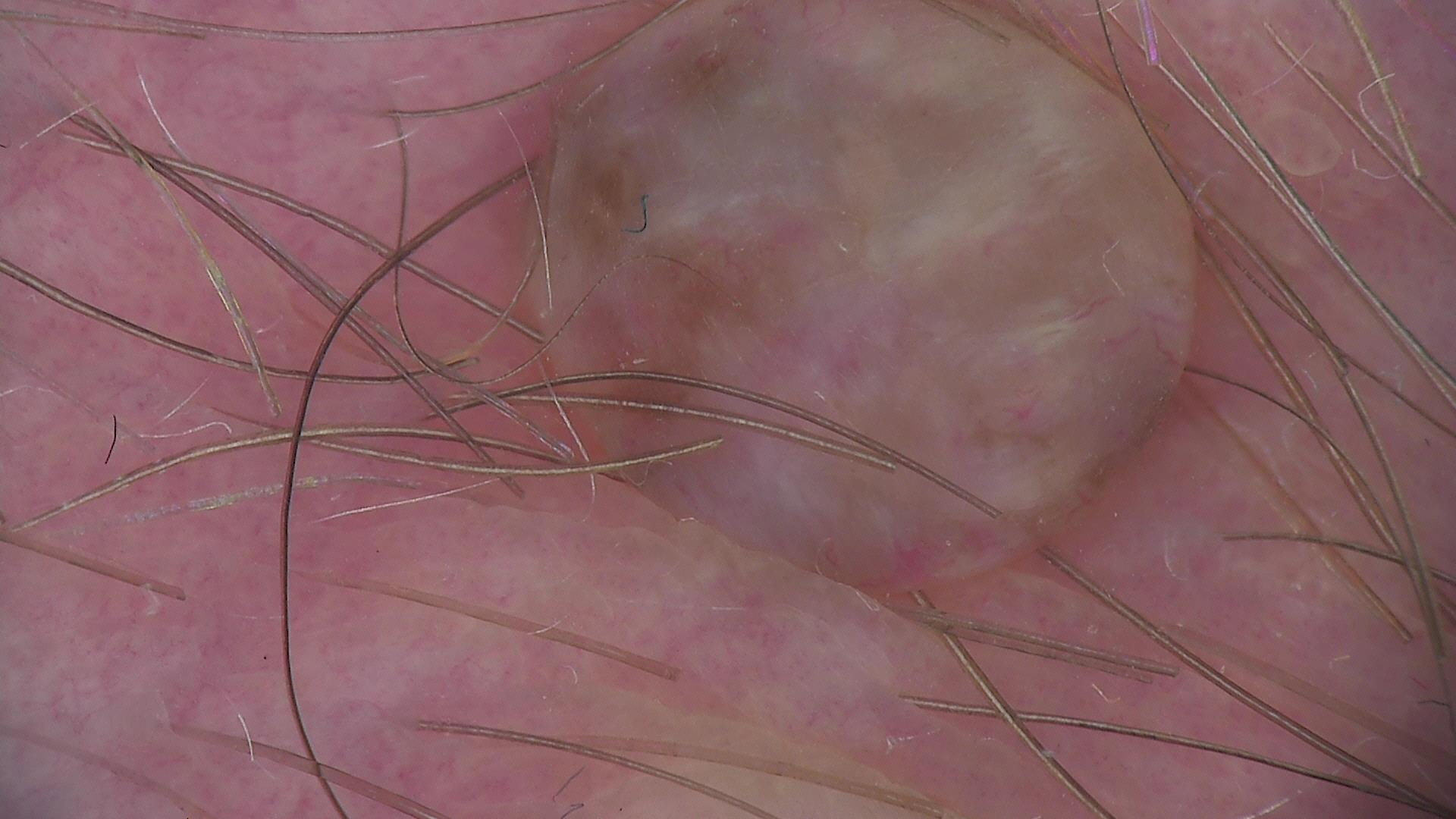The architecture is that of a banal lesion. The diagnosis was a dermal nevus.